A clinical photo of a skin lesion taken with a smartphone; a male patient 55 years of age; history notes prior skin cancer (patient or family) and no tobacco use; Fitzpatrick phototype III:
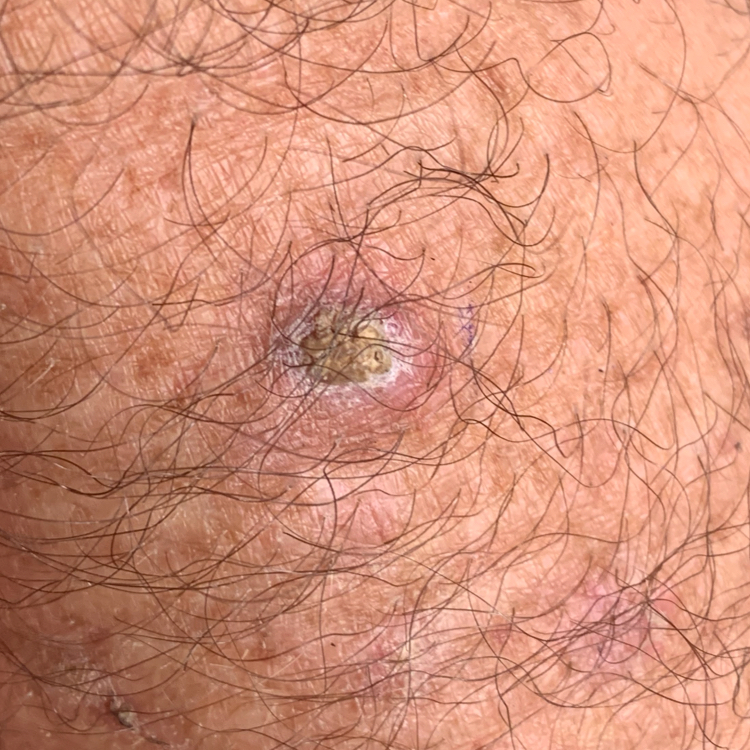Confirmed on histopathology as a lesion with uncertain malignant potential — an actinic keratosis.